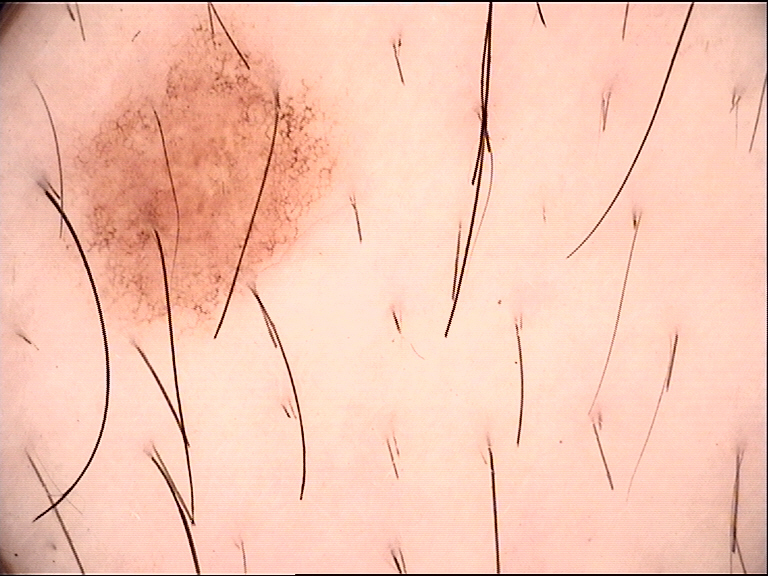Q: What is this lesion?
A: dysplastic junctional nevus (expert consensus)